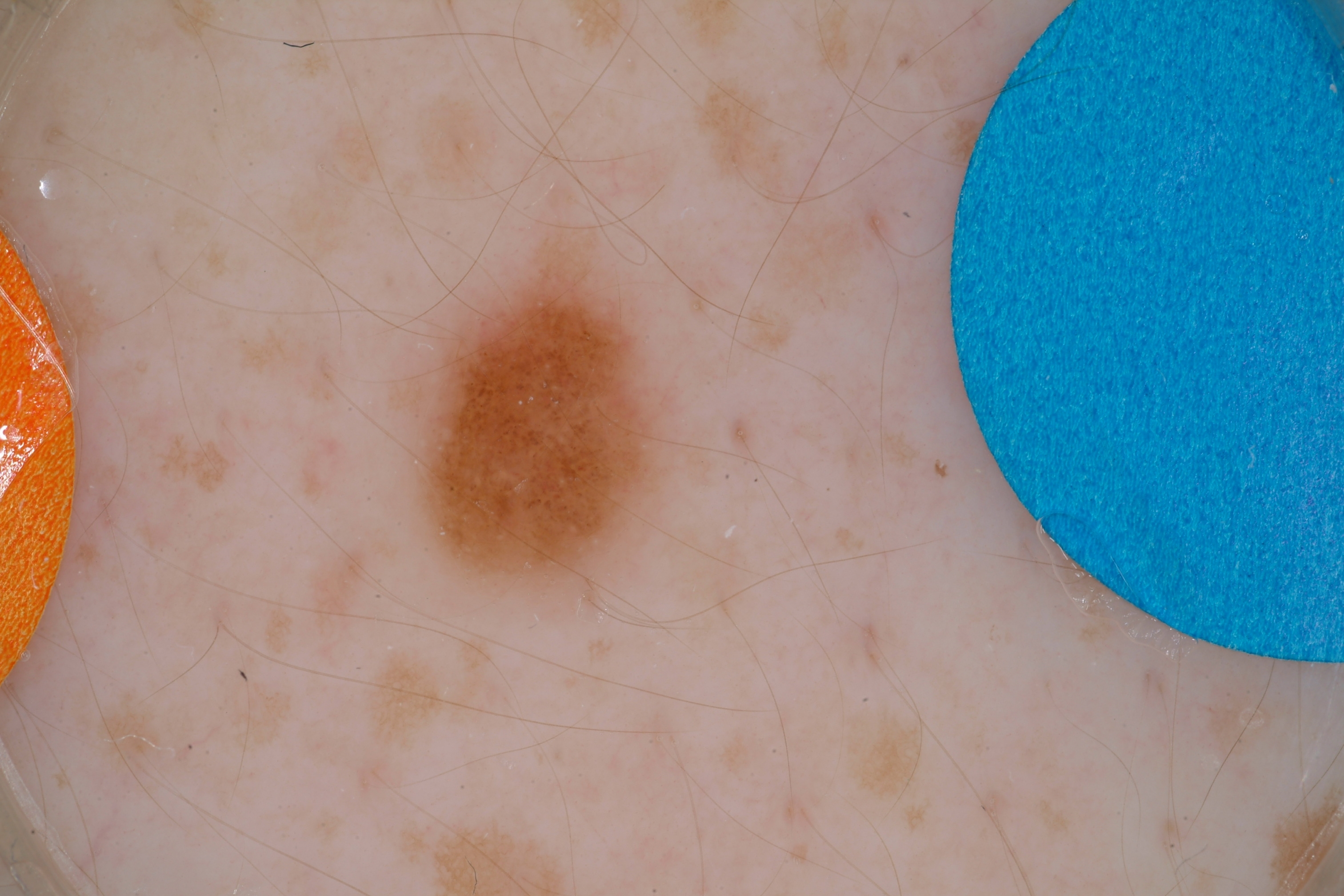Summary:
Dermoscopy of a skin lesion. The subject is a male aged around 15. In (x1, y1, x2, y2) order, the visible lesion spans 405 239 661 587. On dermoscopy, the lesion shows globules.
Assessment:
Consistent with a melanocytic nevus, a benign lesion.